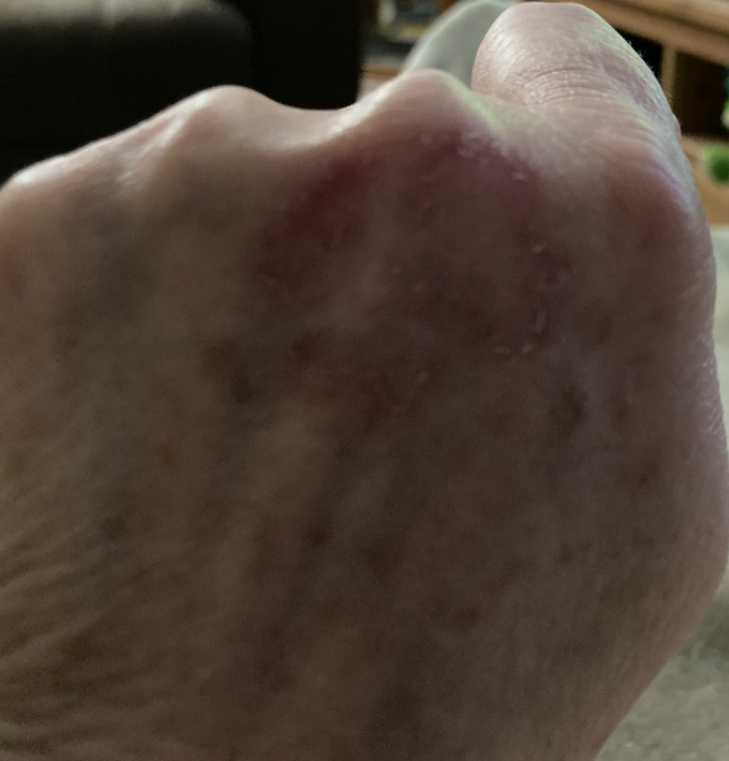Findings:
On remote dermatologist review, Tinea and Eczema were considered with similar weight; less likely is Psoriasis.